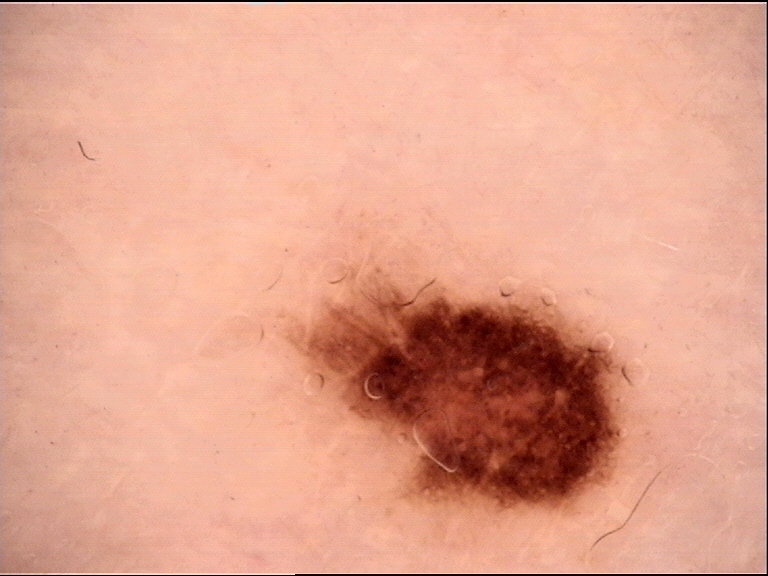diagnosis:
  name: dysplastic junctional nevus
  code: jd
  malignancy: benign
  super_class: melanocytic
  confirmation: expert consensus